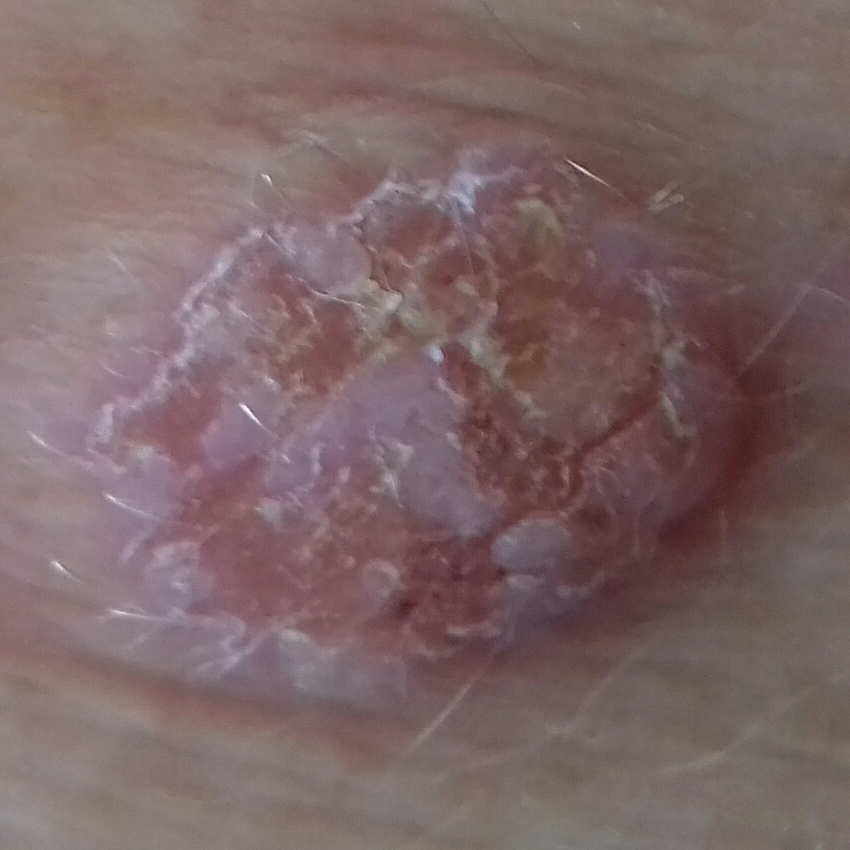| field | value |
|---|---|
| subject | male, aged 83 |
| image type | clinical photograph |
| reported symptoms | itching, elevation |
| diagnosis | squamous cell carcinoma (biopsy-proven) |